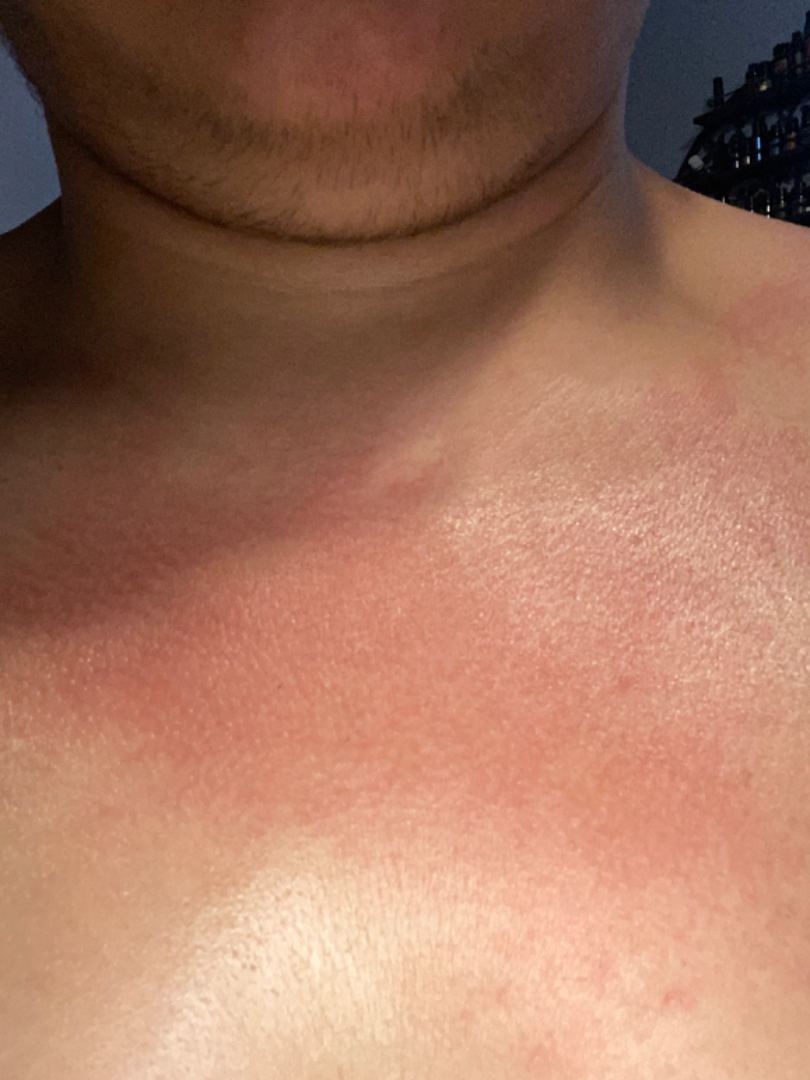Findings: The reviewing dermatologist was unable to assign a differential diagnosis from the image. Background: The lesion is described as flat. No constitutional symptoms were reported. Present for about one day. A close-up photograph. Self-categorized by the patient as a rash. The lesion involves the front of the torso. The lesion is associated with enlargement, itching and burning.